The photograph was taken at a distance: 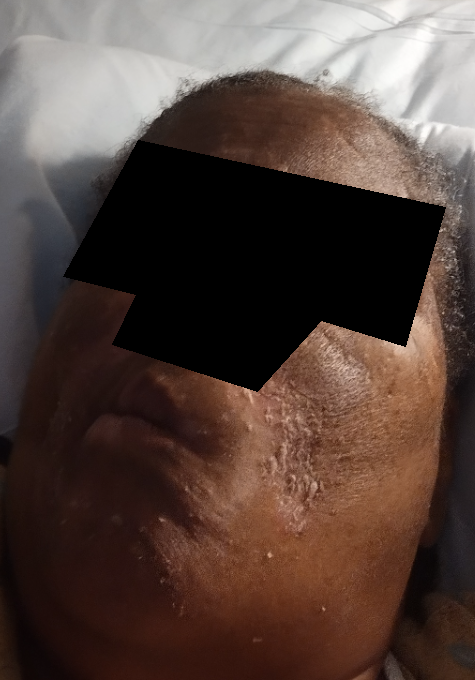assessment = could not be assessed.